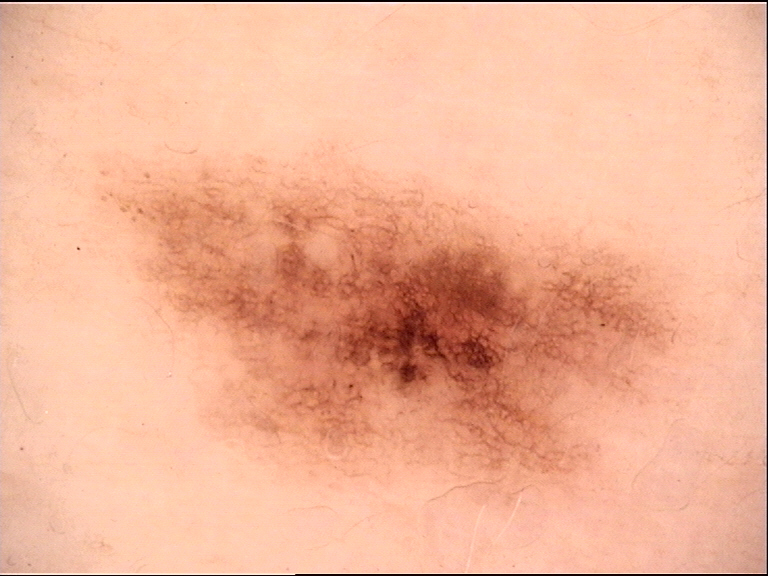label = dysplastic junctional nevus (expert consensus).